A dermatoscopic image of a skin lesion — 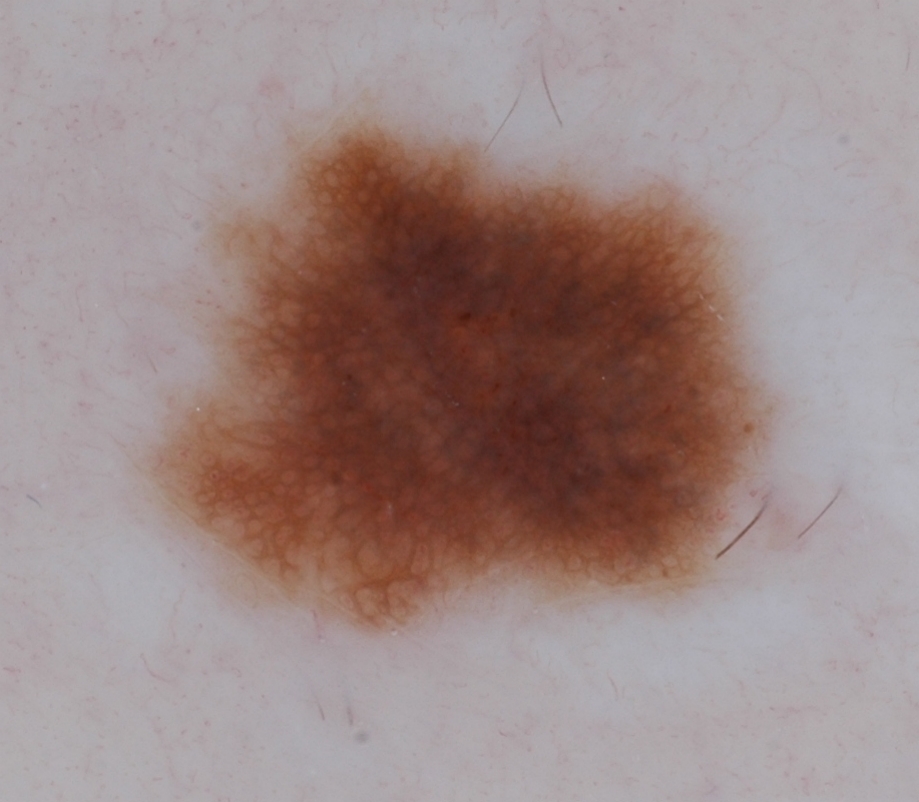The lesion takes up a large portion of the image. The dermoscopic pattern shows globules and pigment network. The lesion is bounded by <box>148, 116, 771, 630</box>. The clinical diagnosis was a melanocytic nevus, a benign skin lesion.